Dermoscopy of a skin lesion · a male patient, roughly 75 years of age.
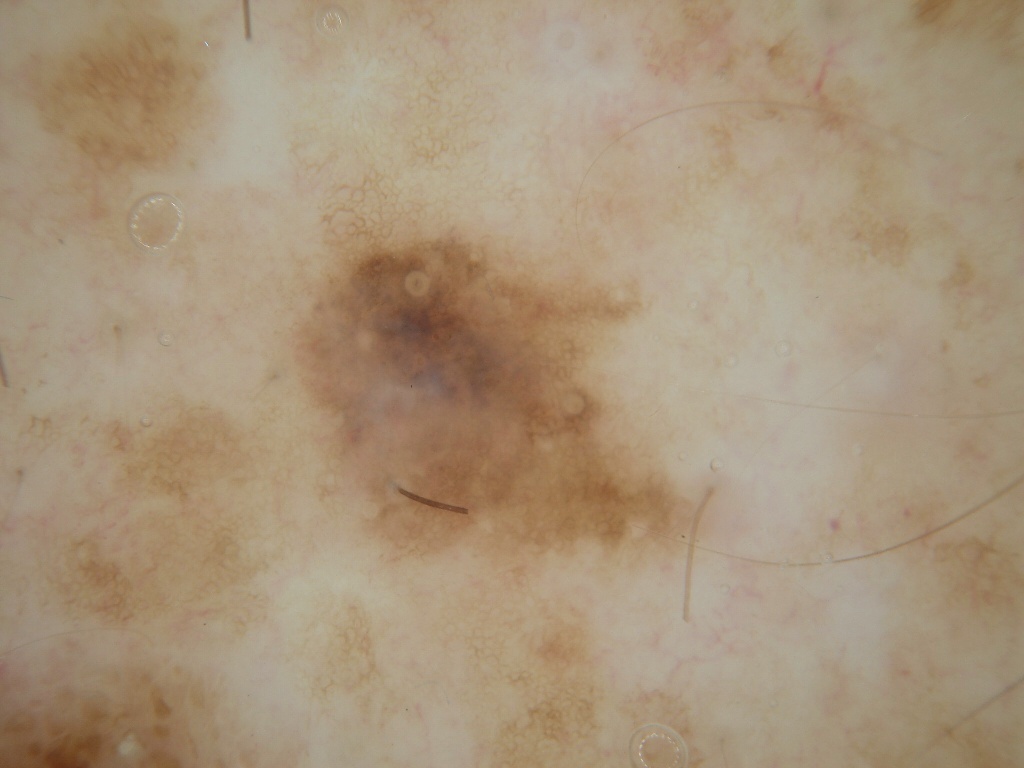Findings:
- bounding box · [288, 216, 703, 578]
- dermoscopic pattern · pigment network; absent: milia-like cysts, negative network, globules, and streaks
- diagnosis · a melanoma